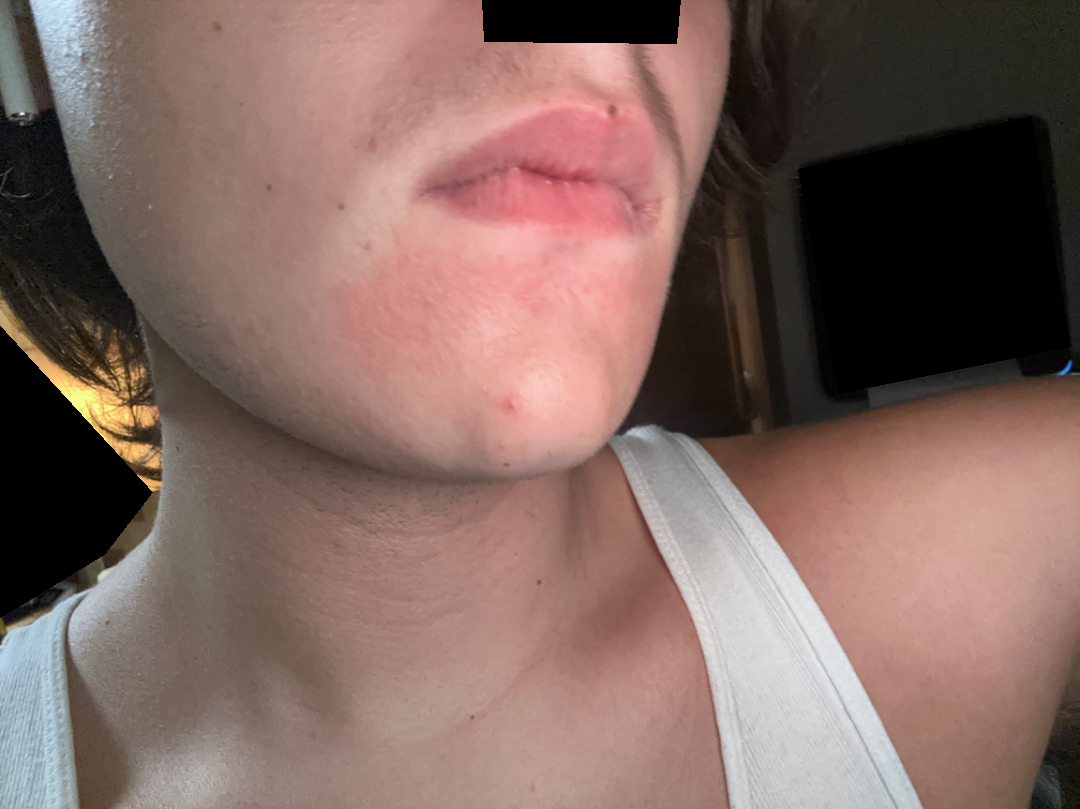patient's own categorization = acne | image framing = at an angle | affected area = head or neck | contributor = male | duration = about one day | symptoms = bothersome appearance | dermatologist impression = Perioral Dermatitis (possible); Allergic Contact Dermatitis (possible); Irritant Contact Dermatitis (possible).